A dermoscopic close-up of a skin lesion; a female subject, in their mid-50s: 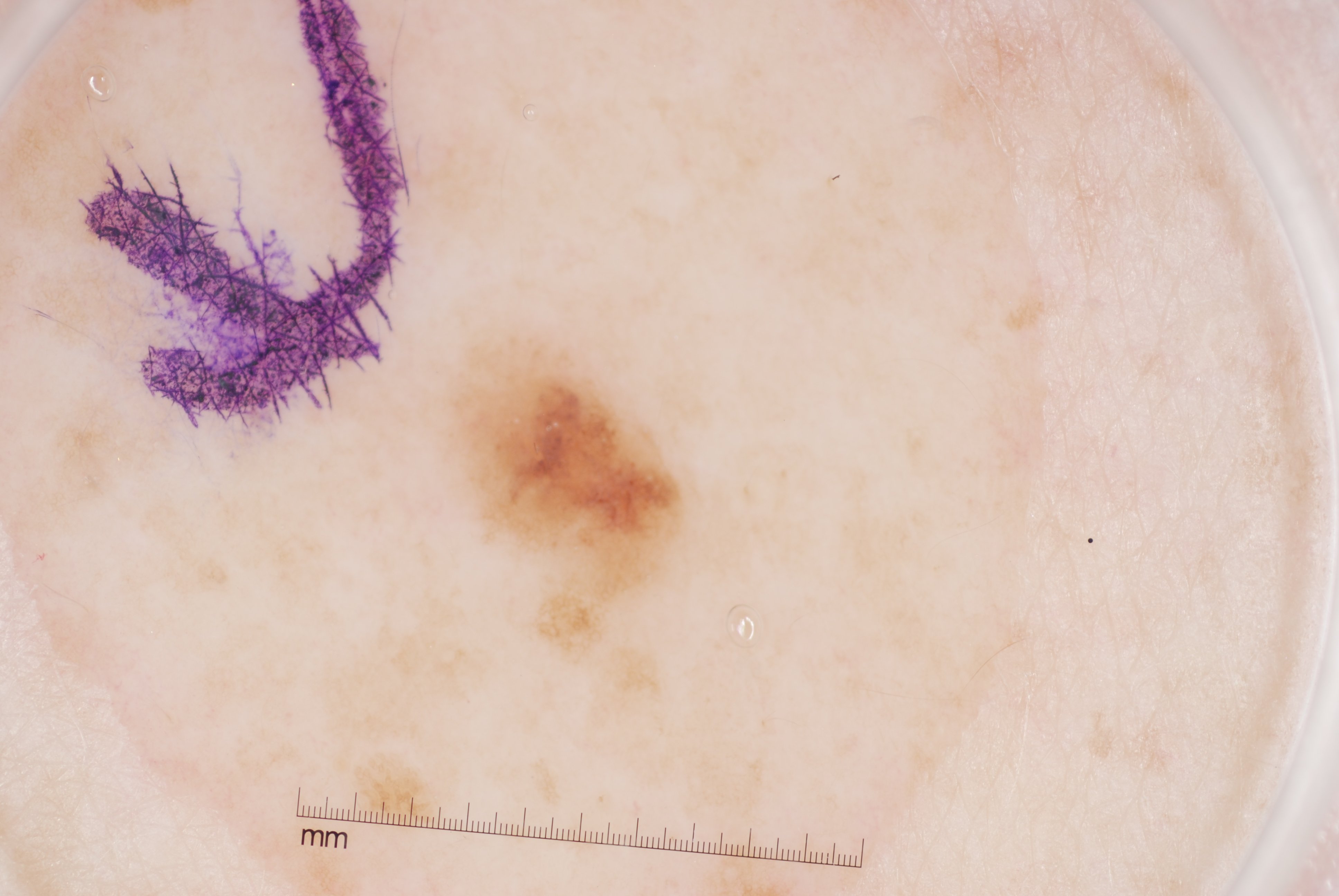Findings:
A small lesion within a wider field of skin. With coordinates (x1, y1, x2, y2), the lesion occupies the region 438/330/702/664. Dermoscopic assessment notes milia-like cysts and pigment network.
Conclusion:
The lesion was assessed as a melanocytic nevus, a benign lesion.